A clinical photo of a skin lesion taken with a smartphone · a male patient age 39 · history notes pesticide exposure, alcohol use, and prior malignancy (patient or family) · the patient is Fitzpatrick phototype II — 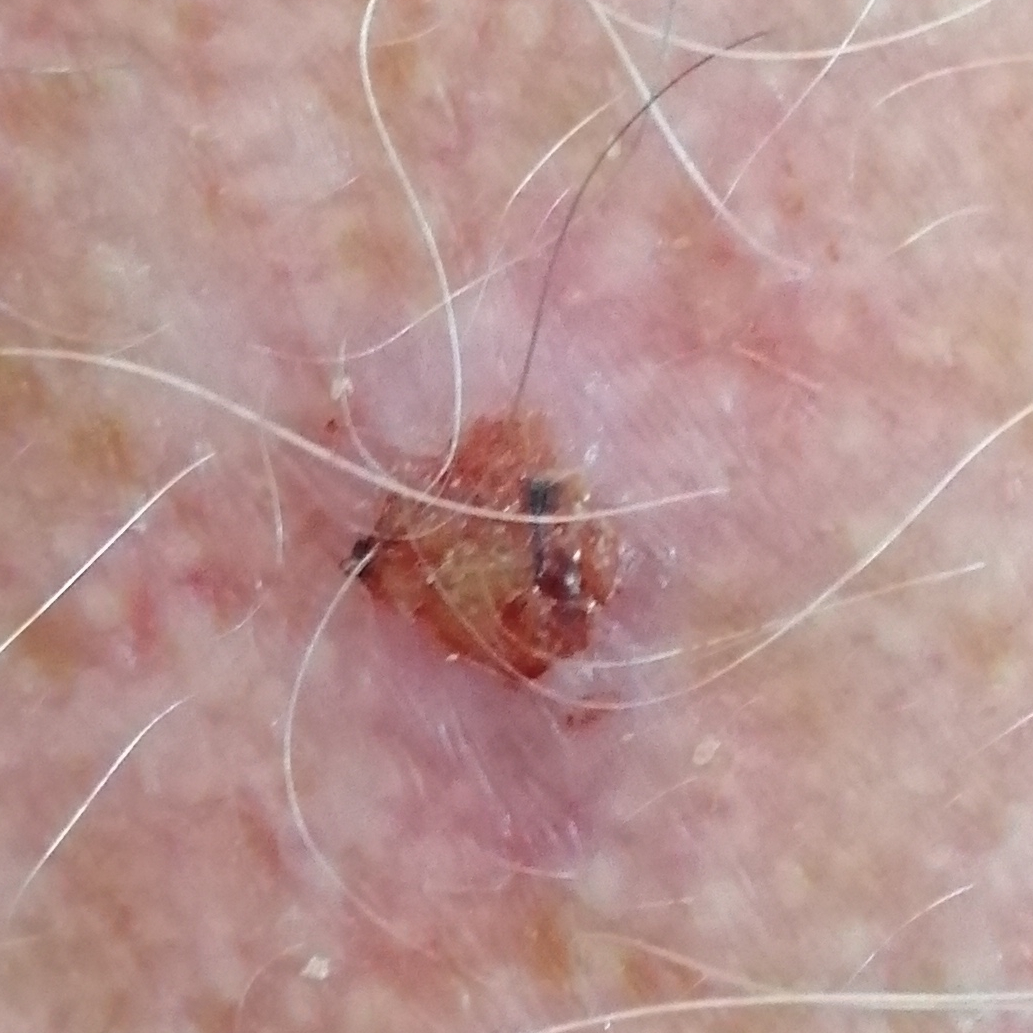<lesion>
<lesion_location>the chest</lesion_location>
<symptoms>
<present>growth, bleeding, pain, itching, elevation</present>
</symptoms>
<diagnosis>
<name>squamous cell carcinoma</name>
<code>SCC</code>
<malignancy>malignant</malignancy>
<confirmation>histopathology</confirmation>
</diagnosis>
</lesion>